A close-up photograph — 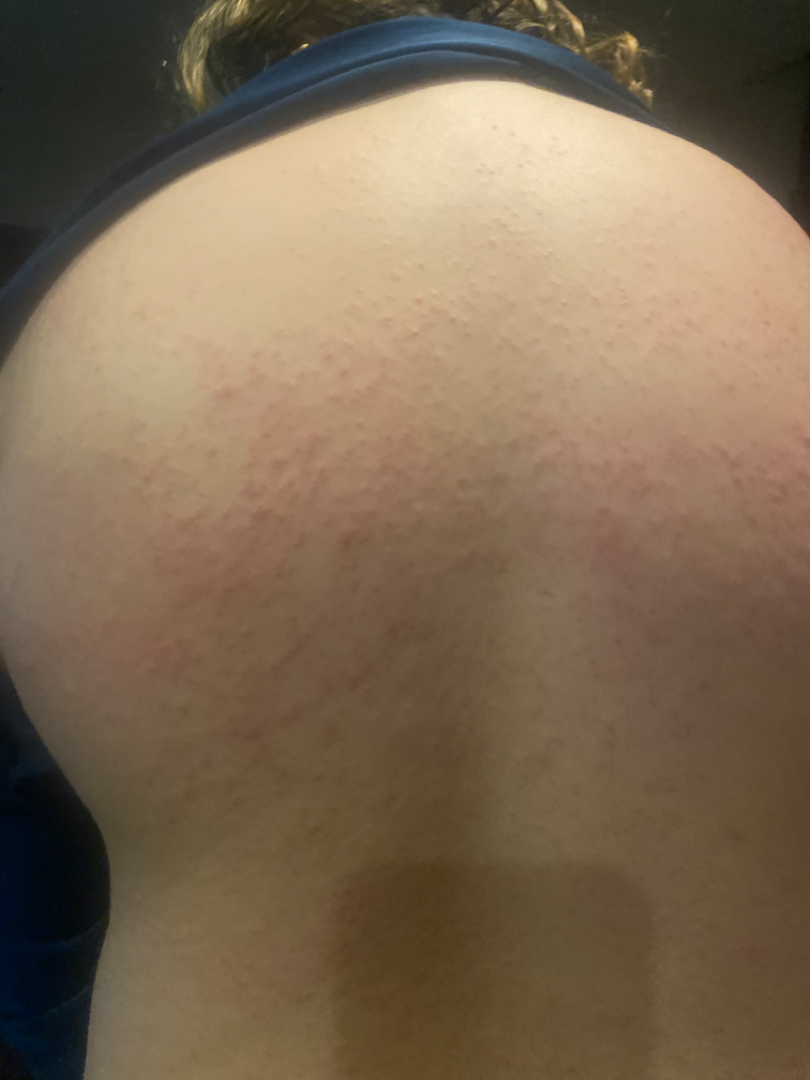symptoms = itching | impression = single-reviewer assessment: the differential, in no particular order, includes Eczema, Hypersensitivity and Allergic Contact Dermatitis.